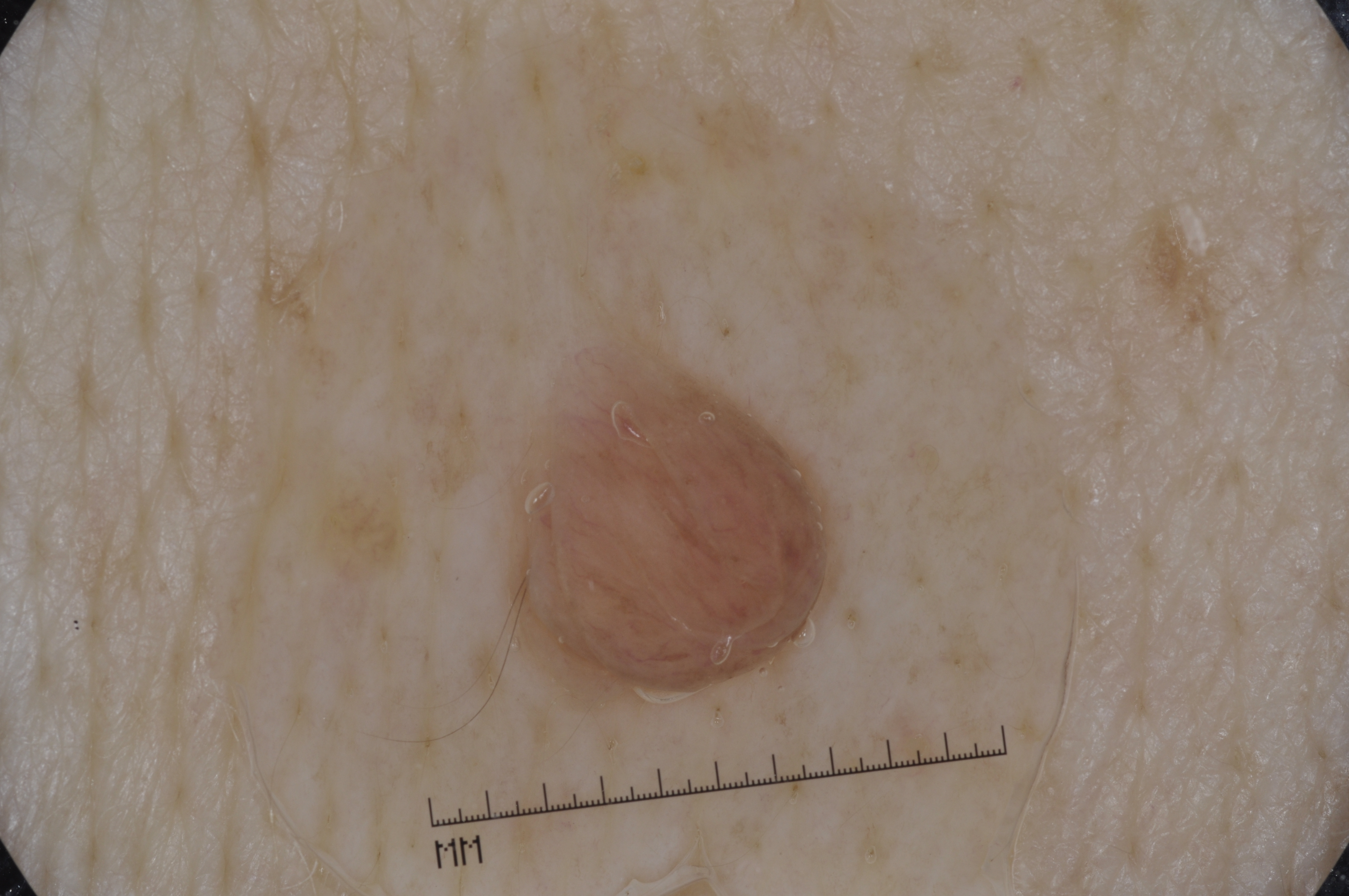A dermoscopic image of a skin lesion.
The lesion is bounded by bbox=[506, 350, 843, 707].
The dermoscopic pattern shows no pigment network, negative network, streaks, or milia-like cysts.
Expert review diagnosed this as a melanocytic nevus.